The affected area is the leg. A close-up photograph: 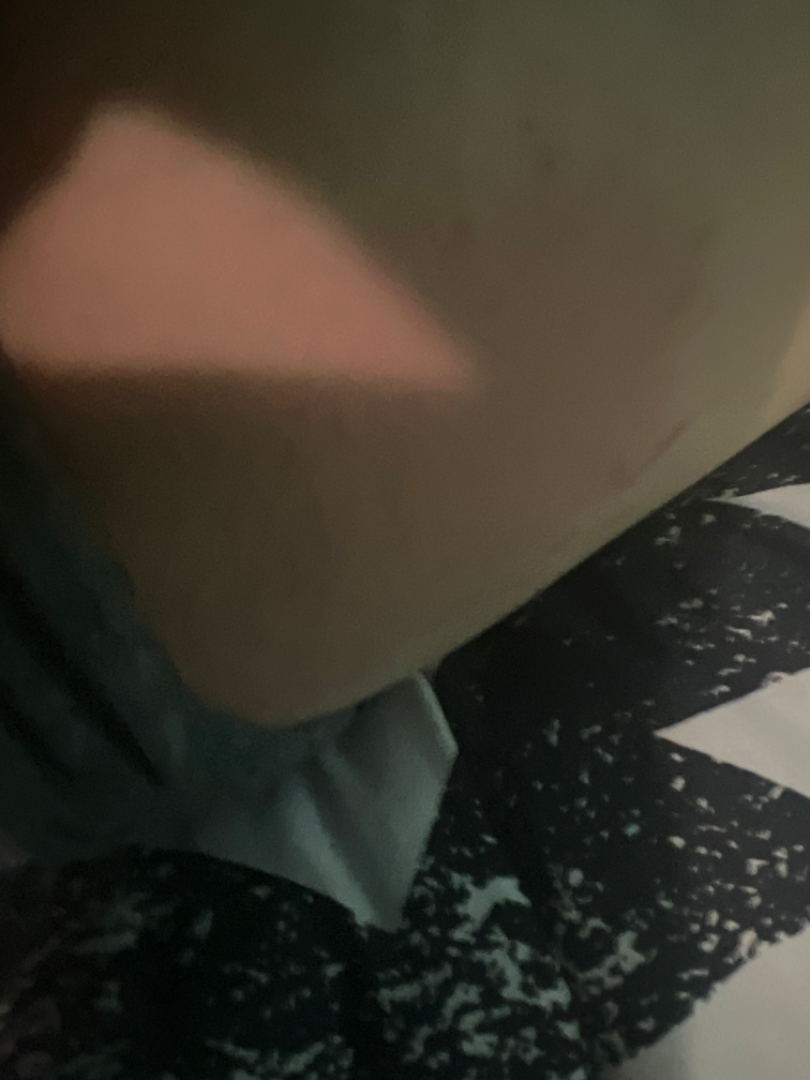The skin condition could not be confidently assessed from this image. Self-categorized by the patient as a rash. The lesion is described as flat. Associated systemic symptoms include joint pain. The contributor reports burning and pain. Skin tone: self-reported Fitzpatrick VI. The condition has been present for about one day.